A dermoscopic view of a skin lesion: 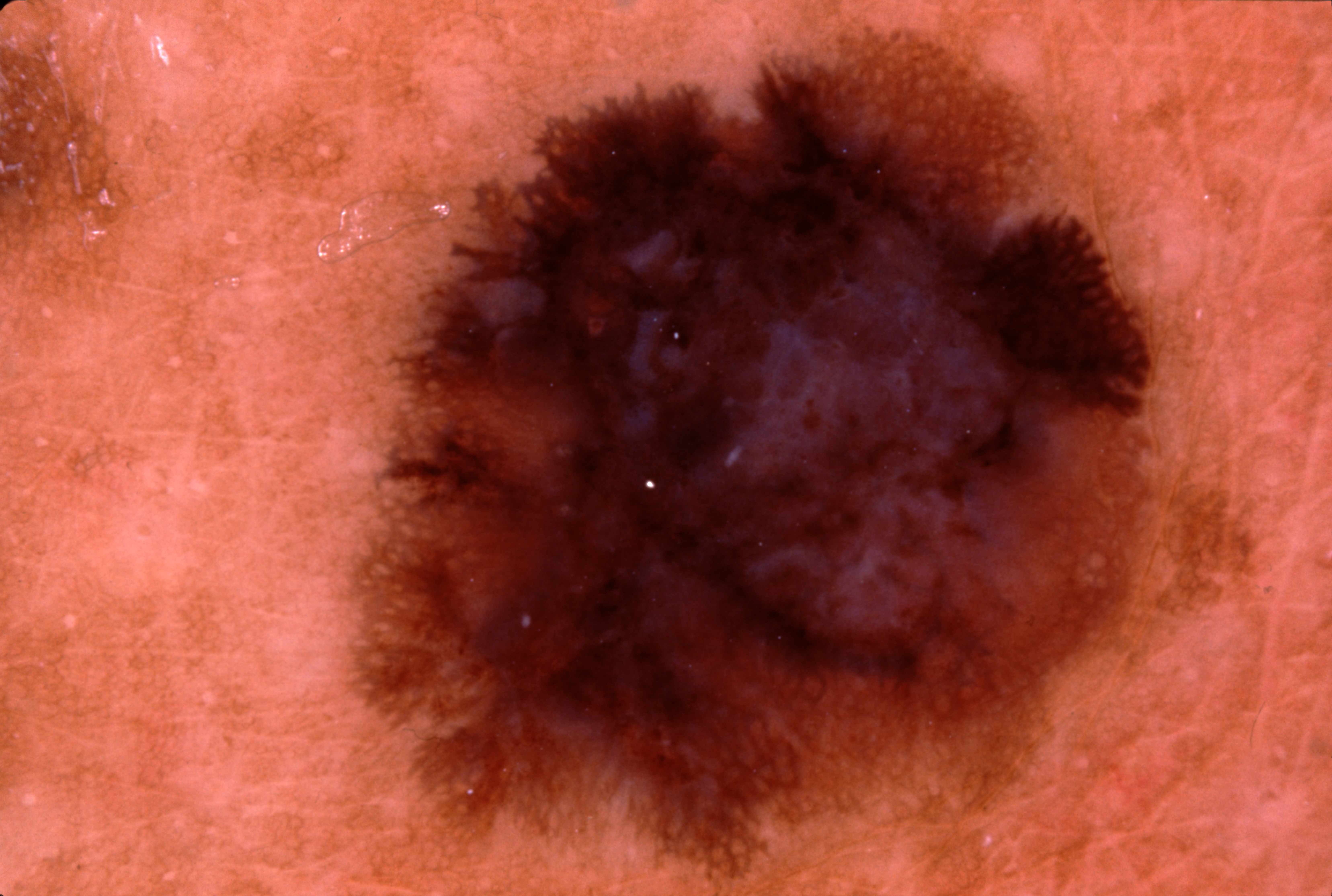| feature | finding |
|---|---|
| dermoscopic pattern | streaks and pigment network; absent: milia-like cysts and negative network |
| lesion location | 354 35 1259 895 |
| diagnostic label | a melanoma, a malignant skin lesion |